A female subject roughly 75 years of age. A contact-polarized dermoscopy image of a skin lesion. The patient was assessed as skin type II — 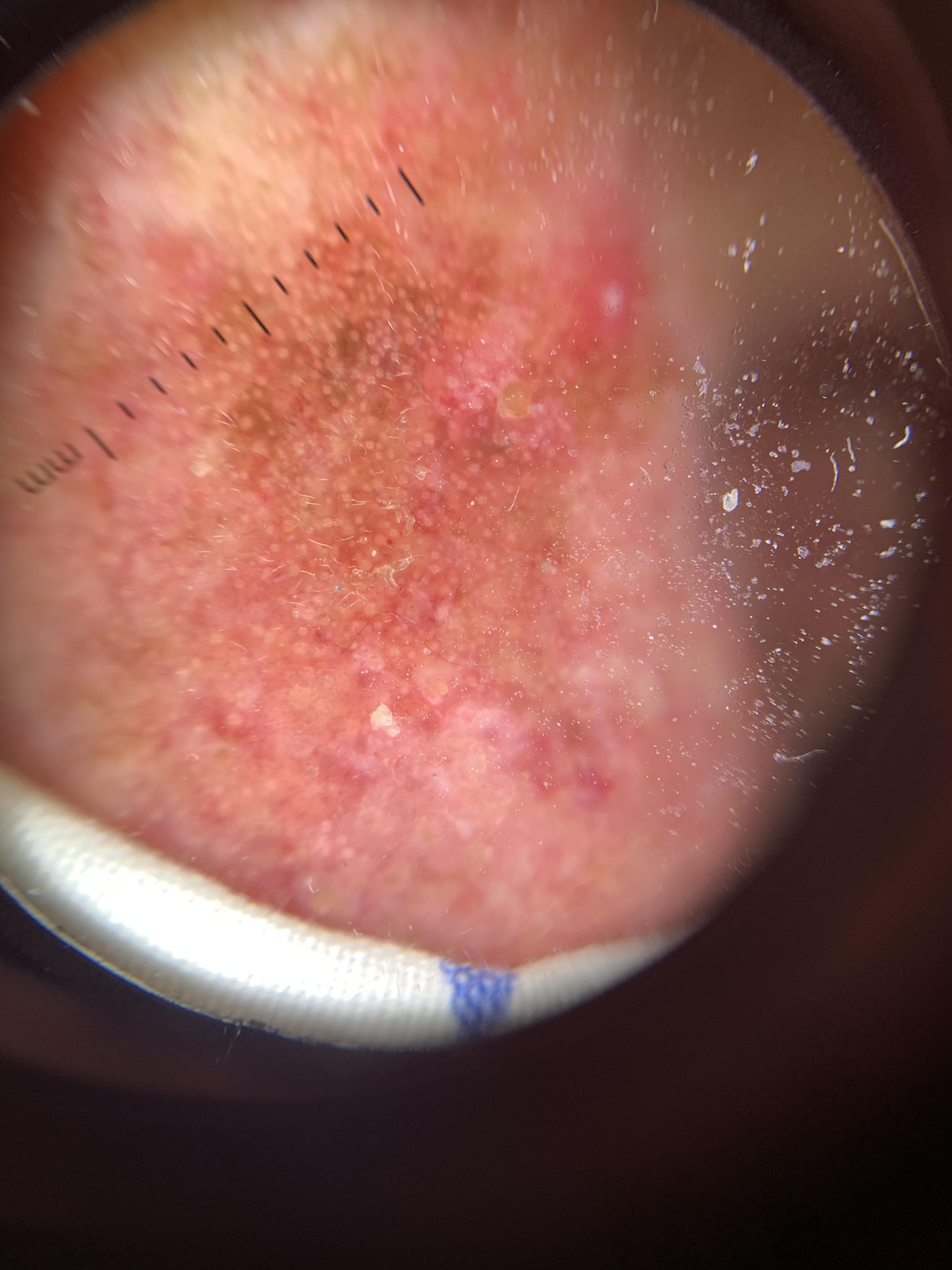The lesion is on the head or neck. Clinically diagnosed as a premalignant, epidermal lesion — a solar or actinic keratosis.